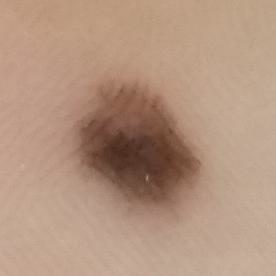The chart notes prior skin cancer (patient or family). A female subject aged 14. Located on a foot. The biopsy diagnosis was a nevus.